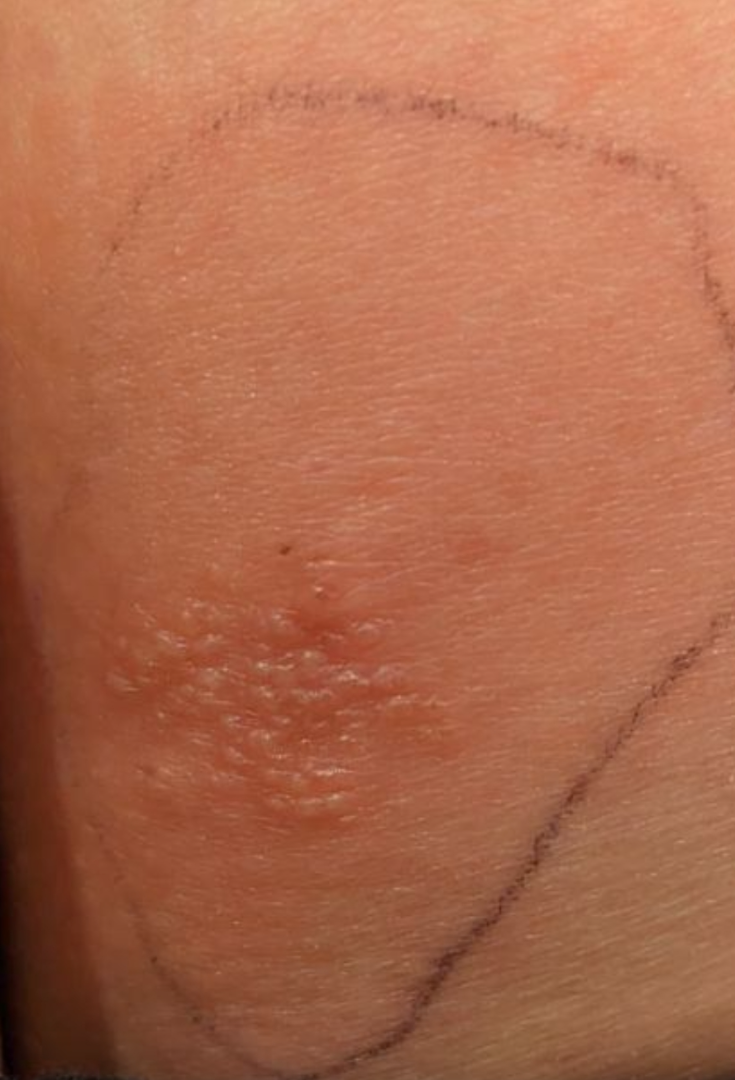image framing: close-up; history: about one day; described texture: raised or bumpy; impression: in keeping with Herpes Simplex.